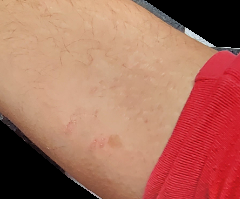{"differential": {"tied_lead": ["Tinea", "Pityriasis rosea"], "unlikely": ["Psoriasis"]}}